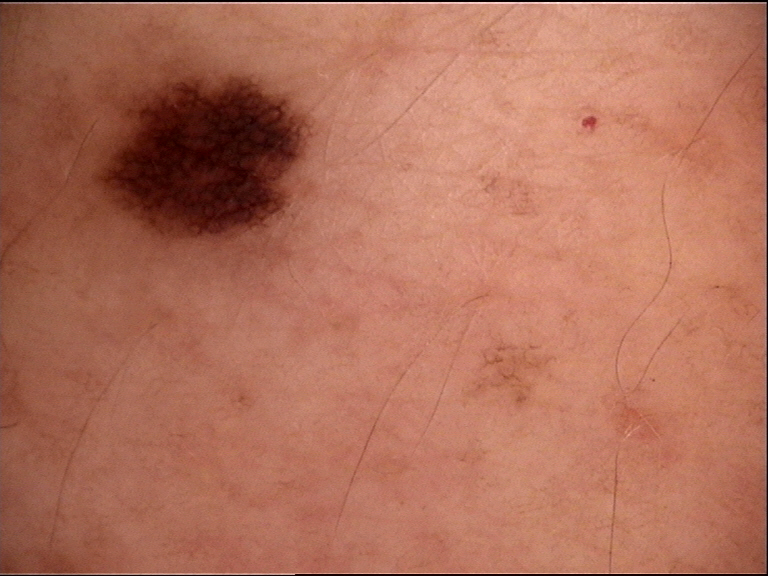Consistent with a dysplastic junctional nevus.